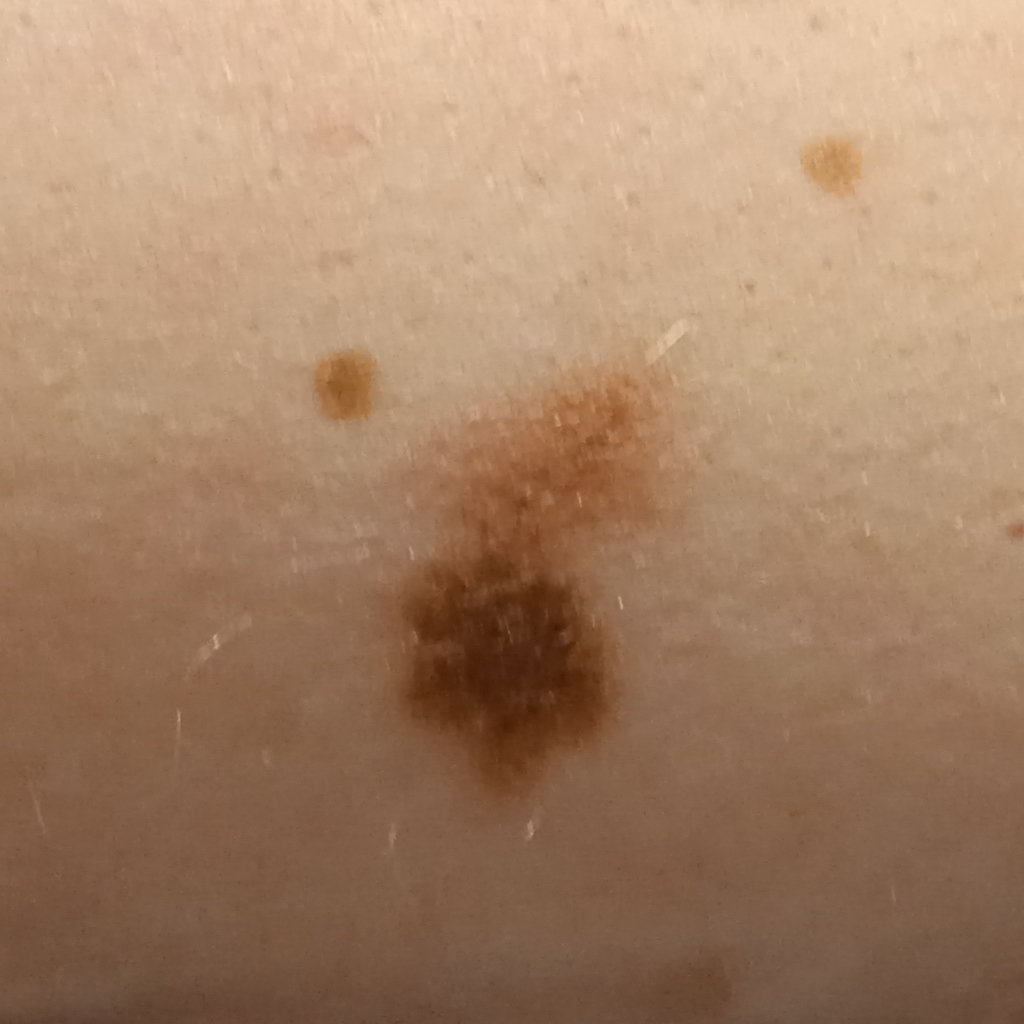The patient describes having numerous moles. A clinical photograph showing a skin lesion. Imaged for a research study, with no referral diagnosis recorded. The patient reports a personal history of cancer, a family history of skin cancer, and a personal history of skin cancer. The lesion is on the torso. The consensus diagnosis for this lesion was a melanoma.